A skin lesion imaged with a dermatoscope.
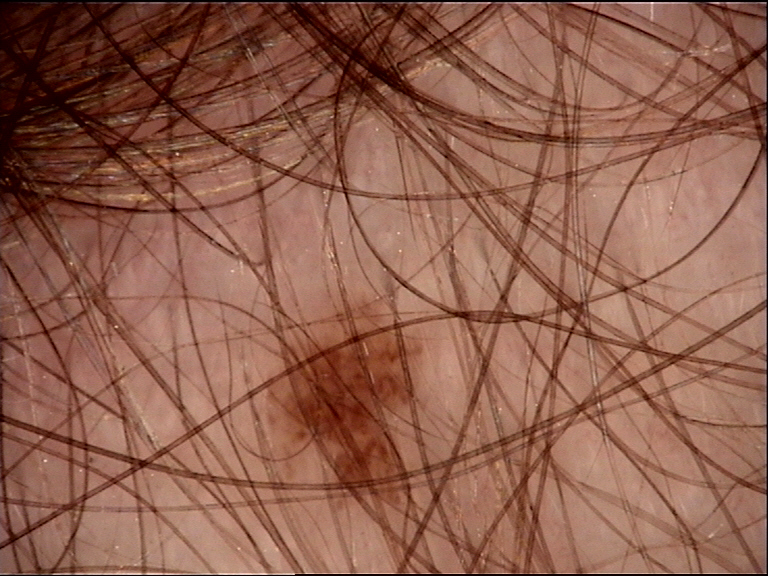category=banal | label=junctional nevus (expert consensus).